A dermoscopy image of a single skin lesion.
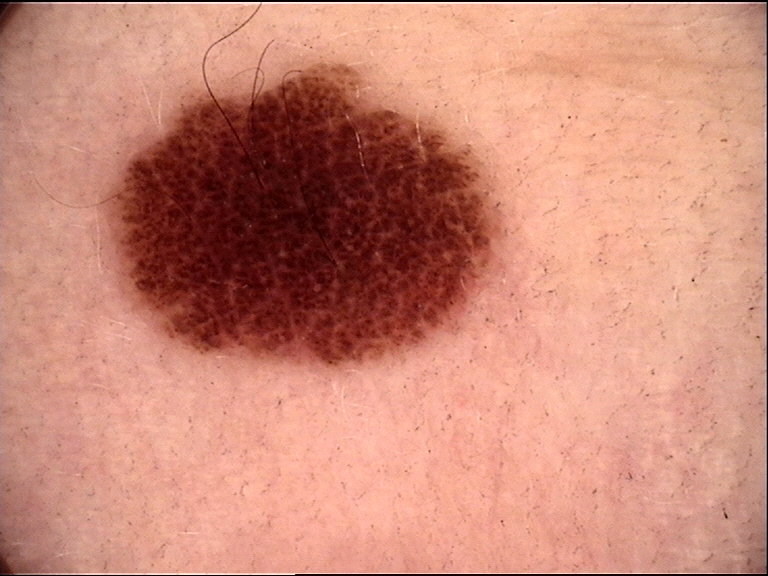Summary: The morphology is that of a banal lesion. Conclusion: Consistent with a compound nevus.